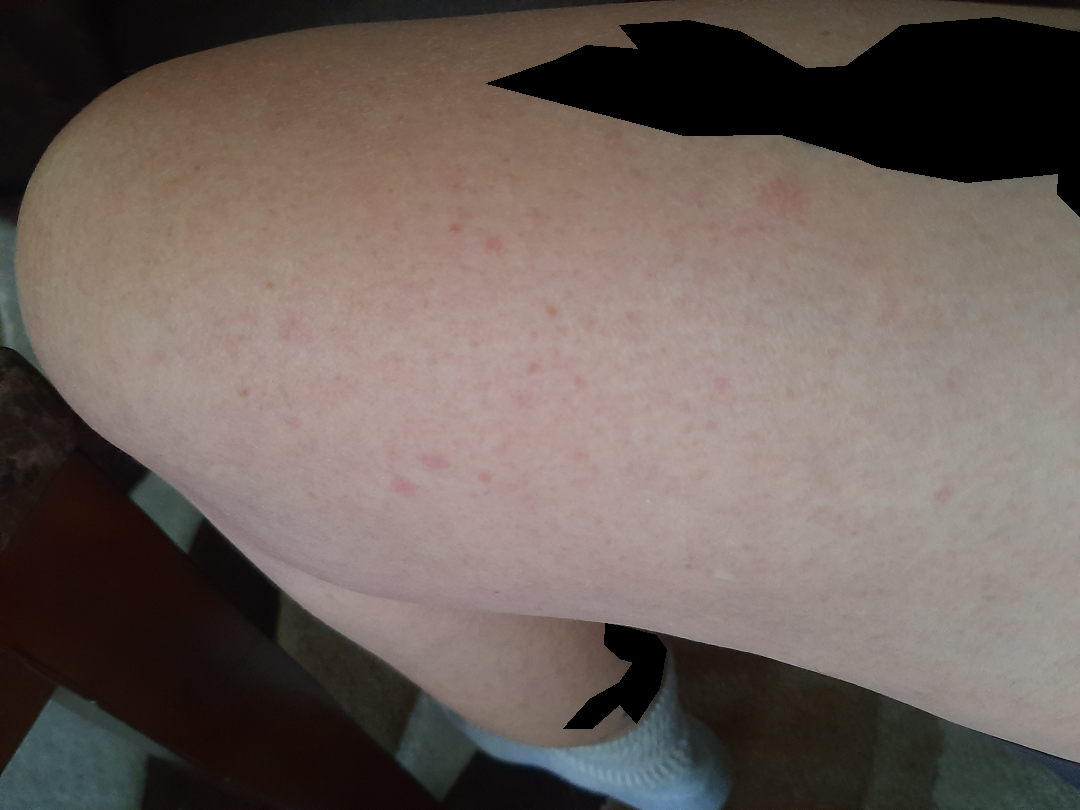The case was difficult to assess from the available photograph. The photo was captured at a distance. Texture is reported as flat. The arm and leg are involved. No relevant systemic symptoms. The condition has been present for one to three months.